A dermoscopic view of a skin lesion — 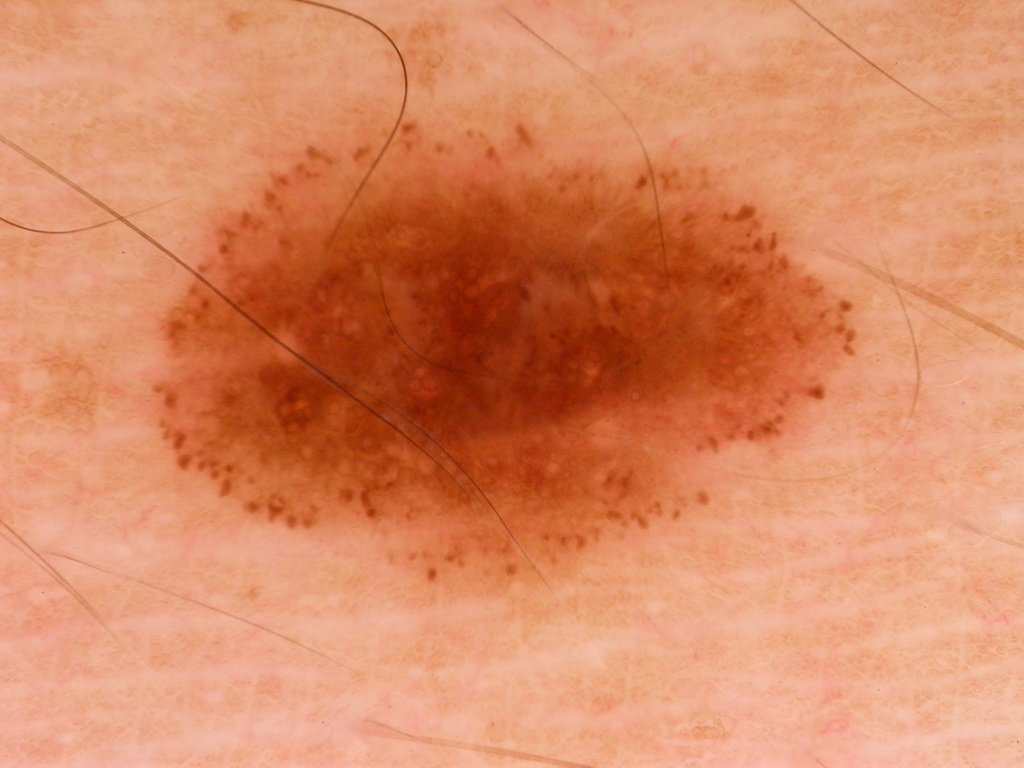dermoscopic features=pigment network and globules
lesion bbox=157 108 867 590
diagnostic label=a melanocytic nevus